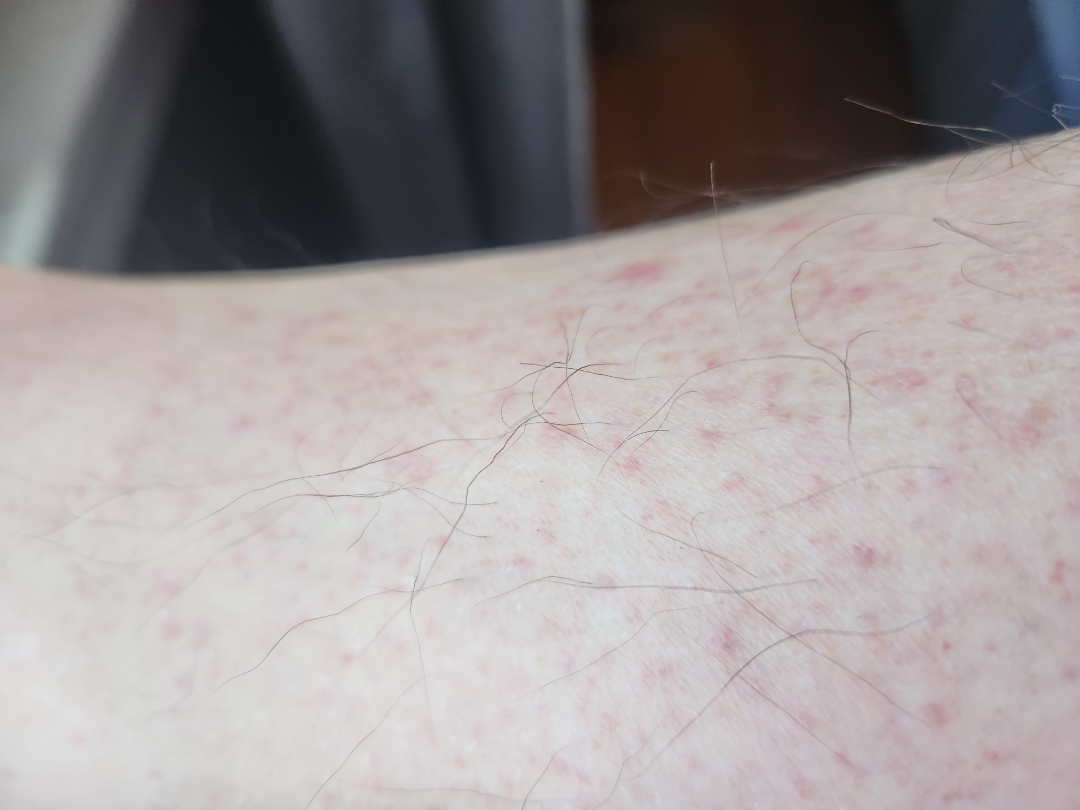Q: Could the case be diagnosed?
A: unable to determine
Q: Image view?
A: close-up
Q: What symptoms does the patient report?
A: bothersome appearance
Q: What is the patient's skin tone?
A: Fitzpatrick II; lay reviewers estimated 1 on the MST
Q: Where on the body?
A: leg and arm
Q: What is the lesion texture?
A: flat